A dermoscopic photograph of a skin lesion.
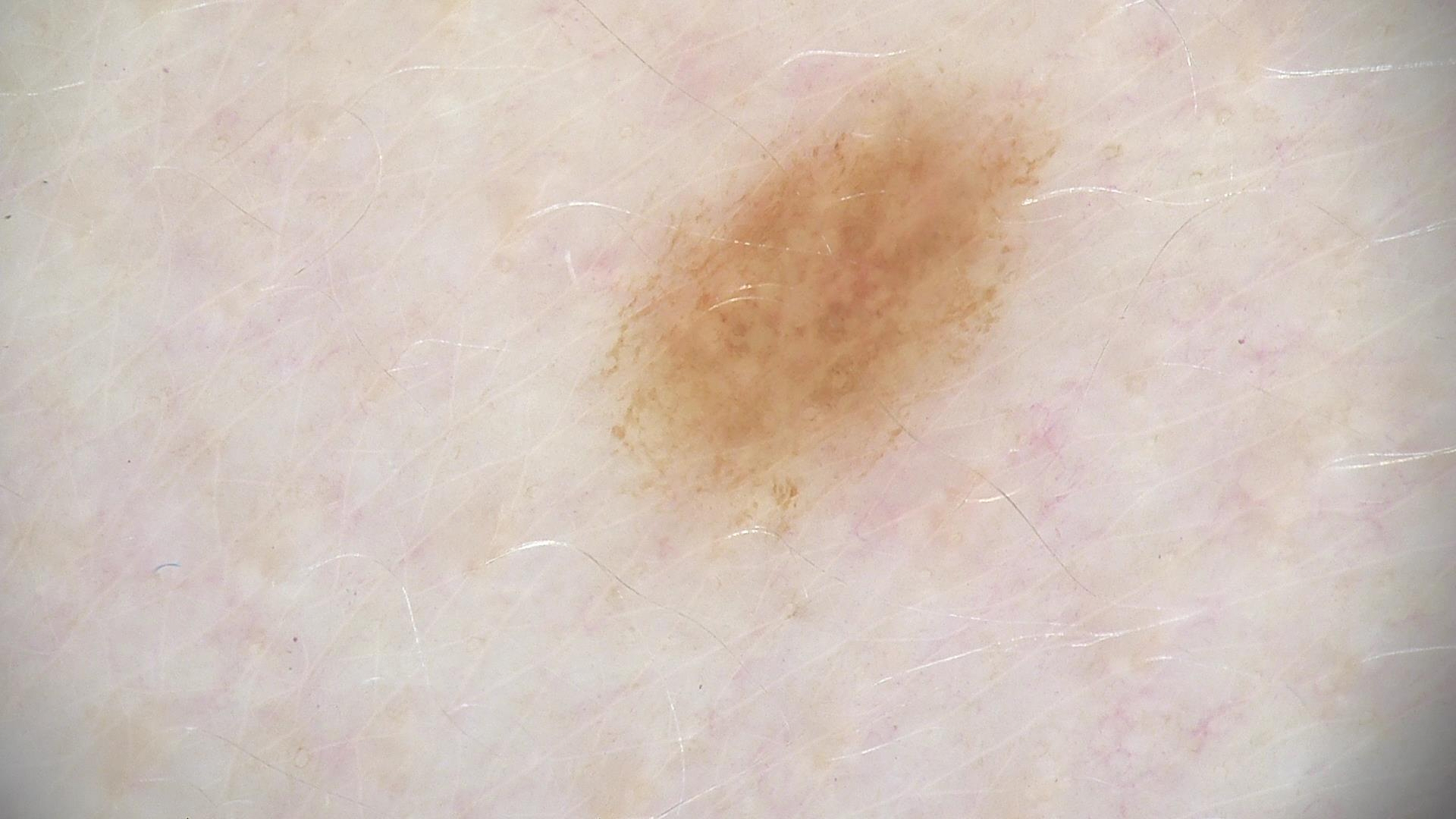Case:
– class — dysplastic junctional nevus (expert consensus)